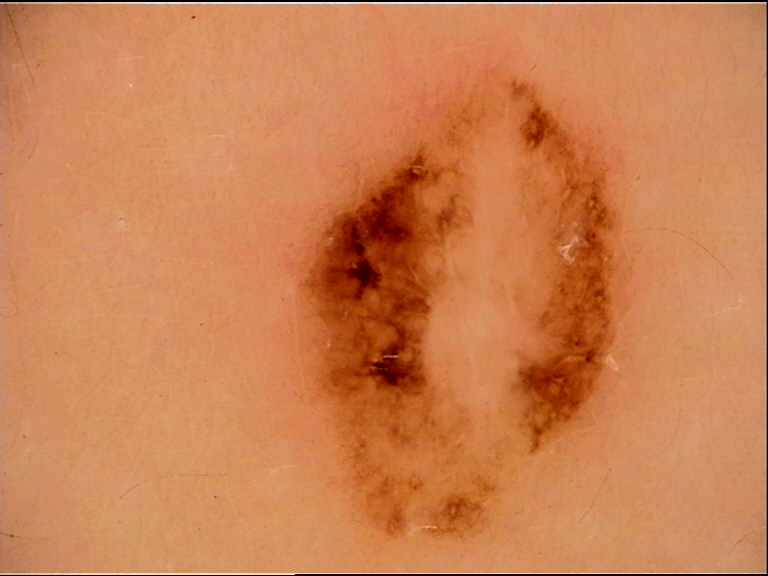imaging=dermatoscopy; pathology=melanoma (biopsy-proven).